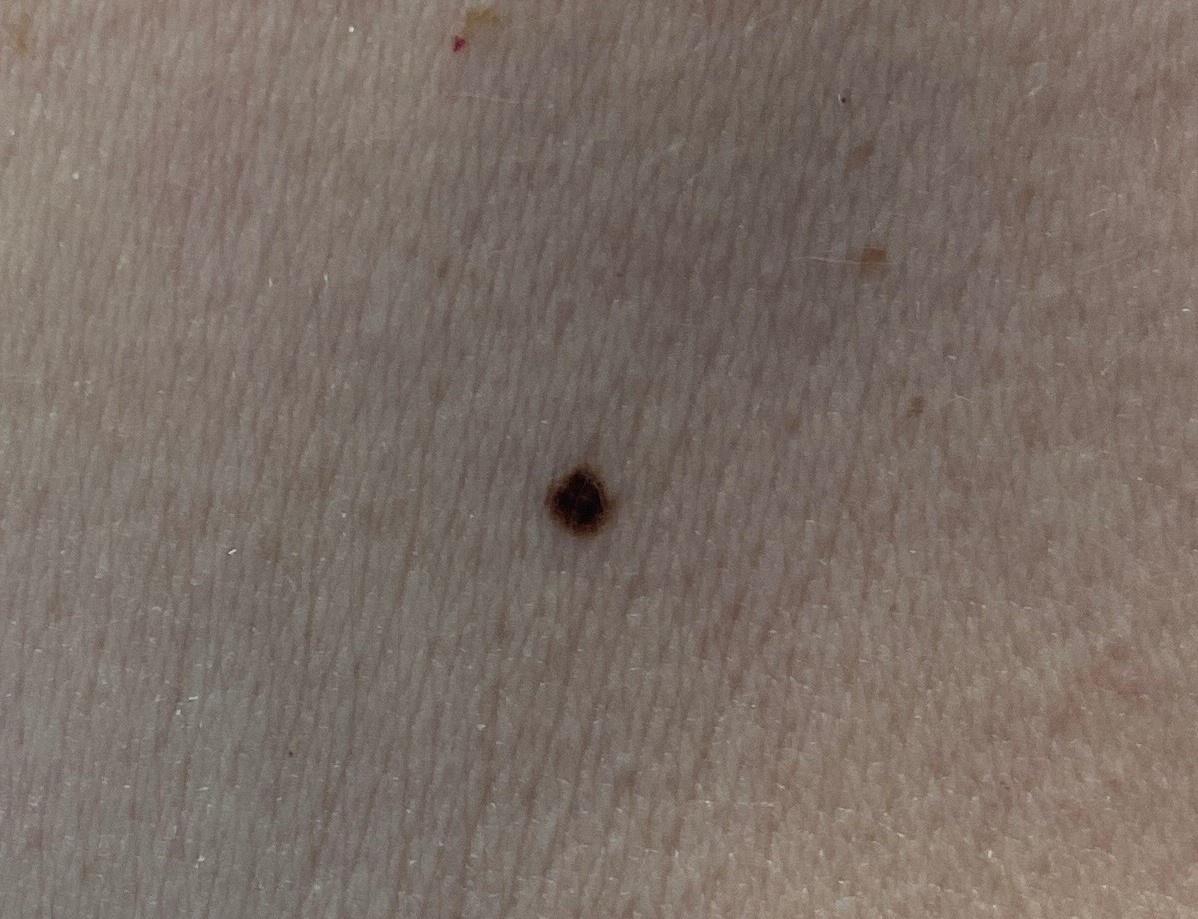A female subject about 70 years old. The chart documents a previous melanoma. The clinical impression was a nevus.